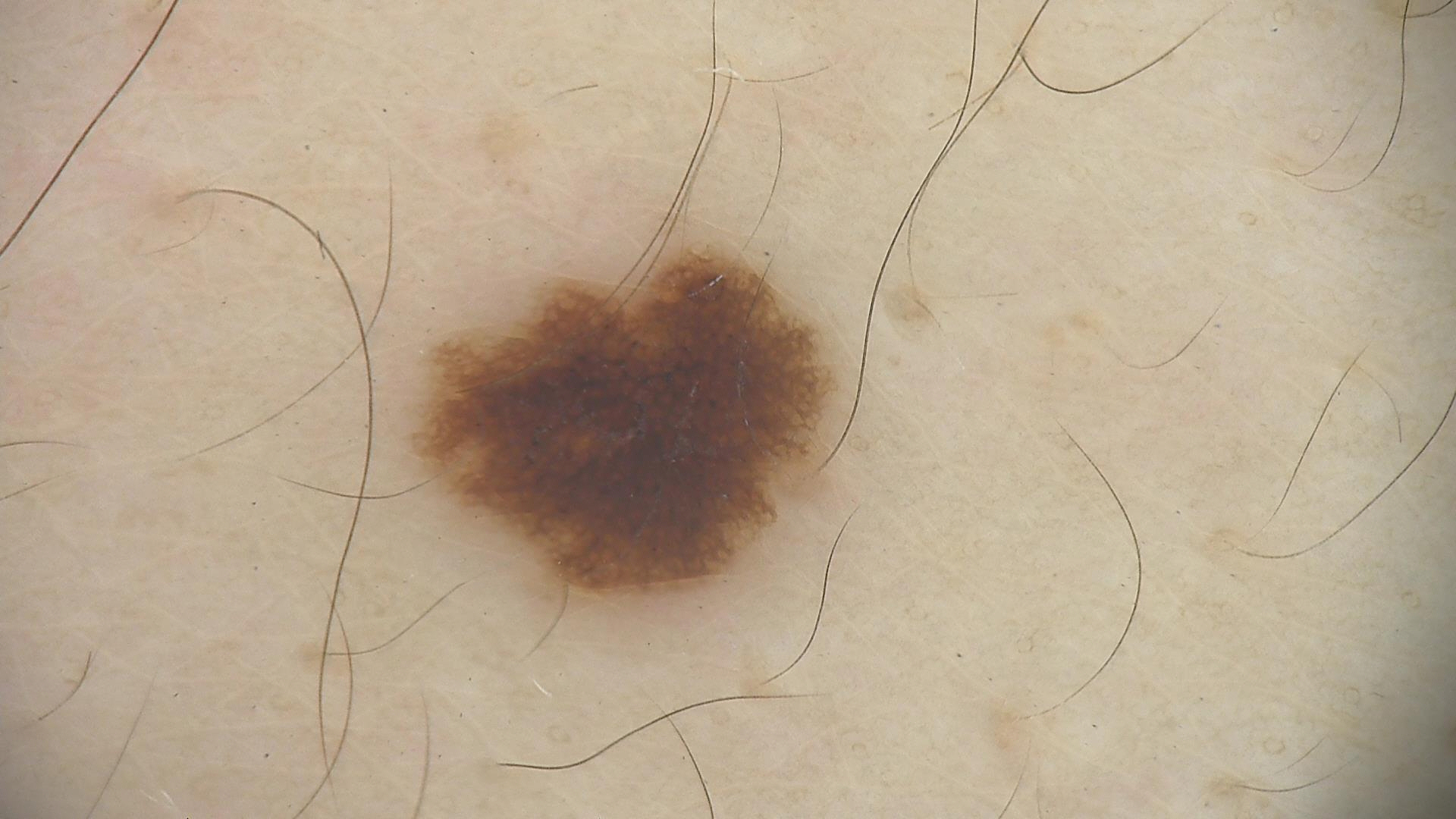A dermoscopic photograph of a skin lesion.
The diagnostic label was a dysplastic junctional nevus.